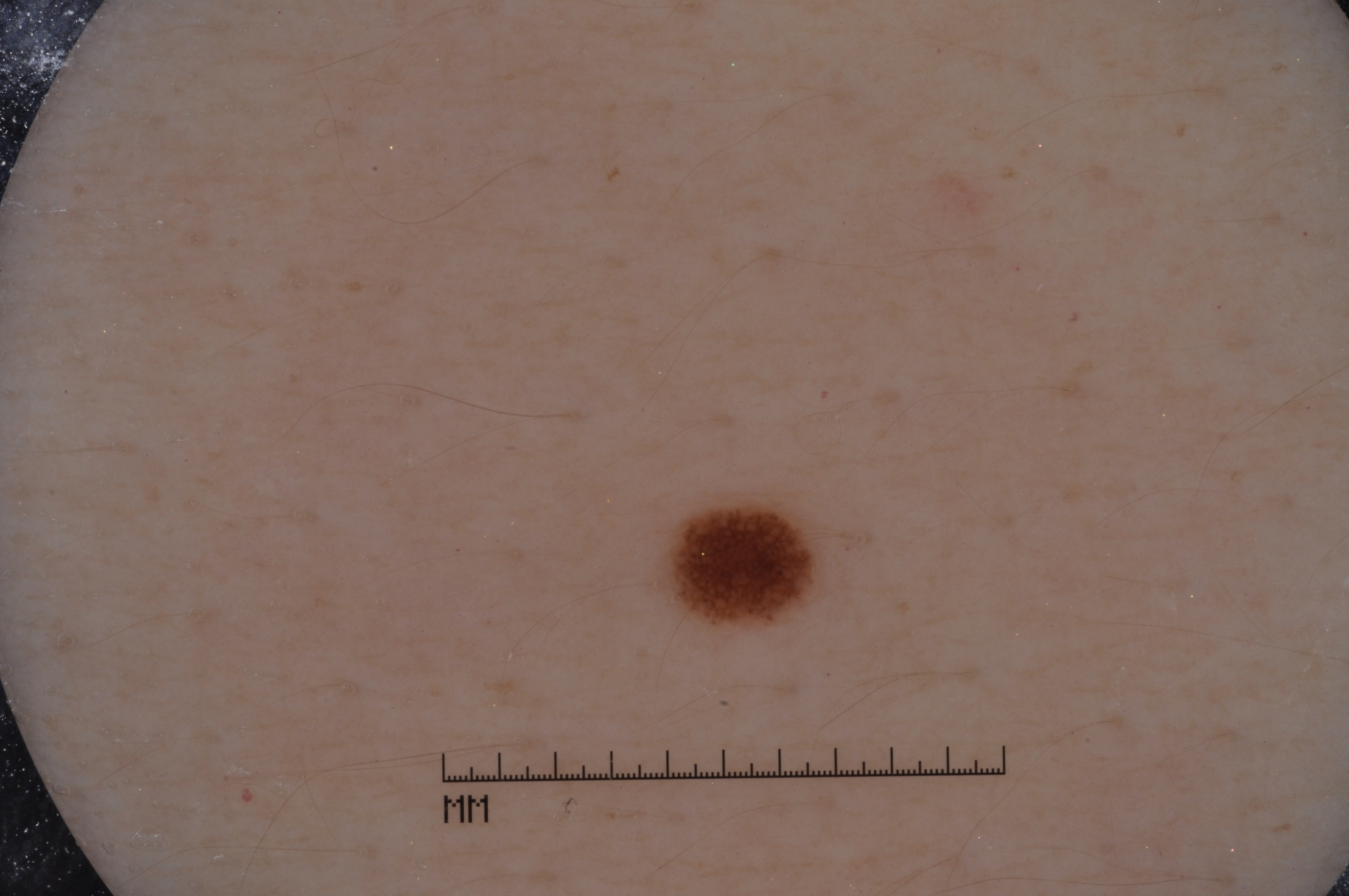subject — female, about 35 years old
modality — dermoscopy of a skin lesion
features — pigment network; absent: streaks, negative network, and milia-like cysts
lesion extent — small
bounding box — (674, 505, 822, 623)
assessment — a melanocytic nevus